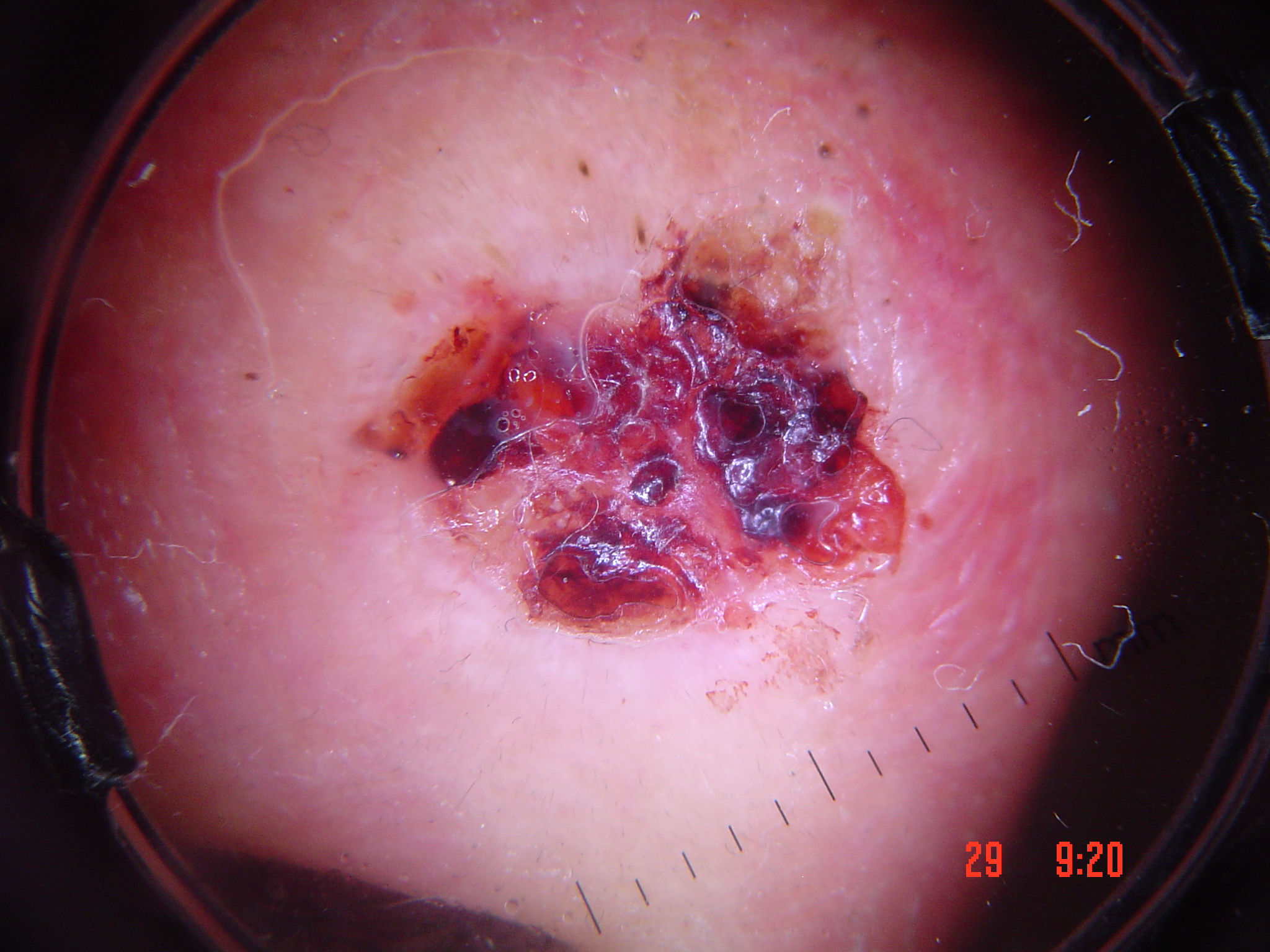A dermoscopic image of a skin lesion. Biopsy-confirmed as a malignant lesion — a squamous cell carcinoma.